A dermatoscopic image of a skin lesion.
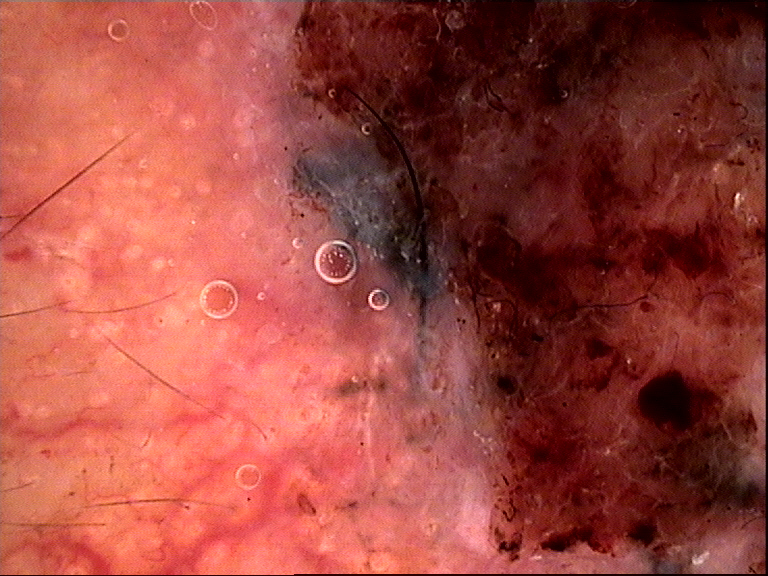category = keratinocytic | class = basal cell carcinoma (biopsy-proven).